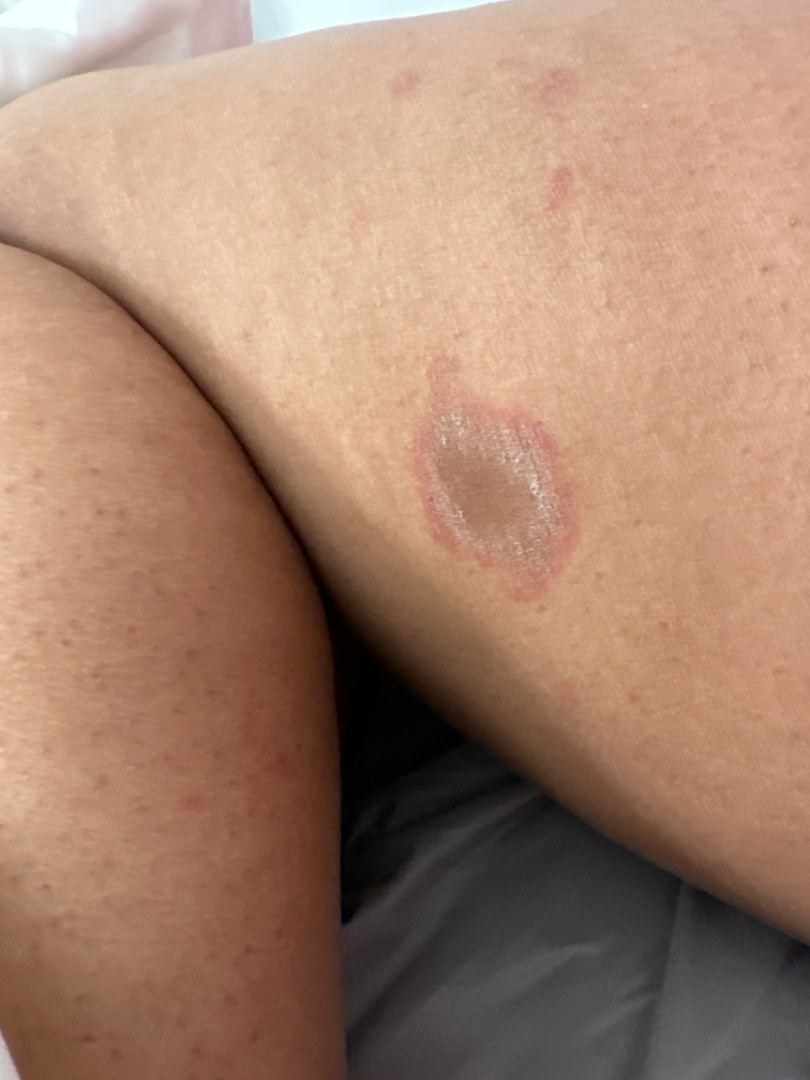Findings:
– patient — female, age 18–29
– anatomic site — leg
– associated systemic symptoms — fatigue
– framing — at a distance
– reported symptoms — bothersome appearance and darkening
– symptom duration — one to three months
– impression — Drug Rash (primary)